An image taken at a distance · the lesion involves the head or neck, top or side of the foot, back of the hand, arm and leg · the subject is male — 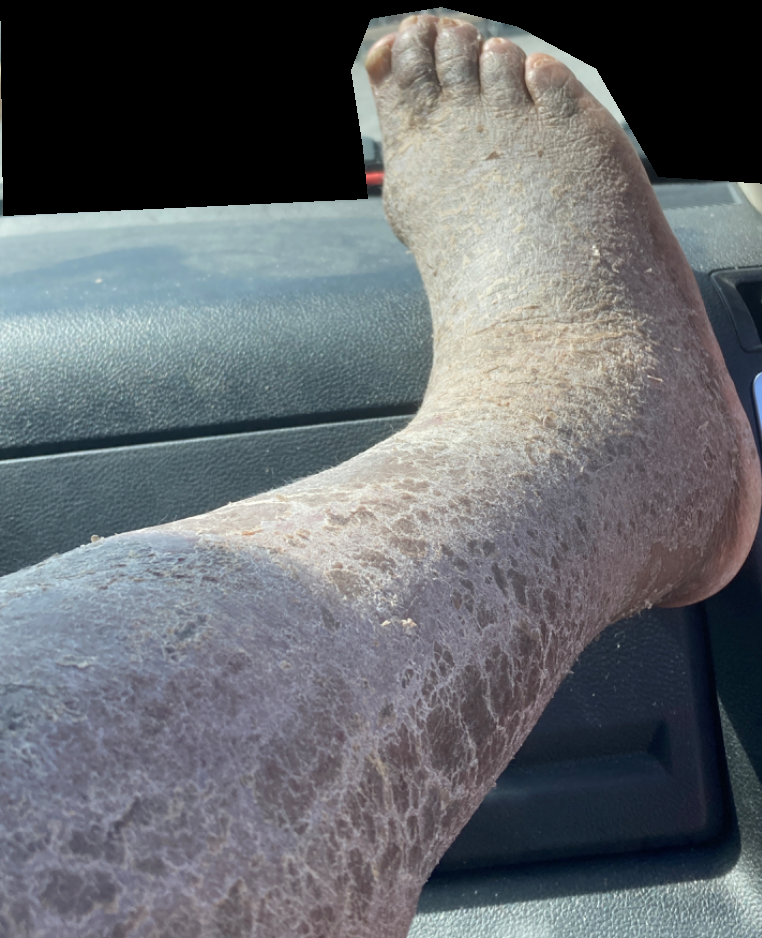| feature | finding |
|---|---|
| systemic symptoms | none reported |
| history | one to three months |
| lesion texture | rough or flaky and fluid-filled |
| skin tone | lay reviewers estimated Monk Skin Tone 1 (US pool) or 2 (India pool) |
| lesion symptoms | bleeding, burning, pain, bothersome appearance, enlargement and itching |
| diagnostic considerations | consistent with Ichthyosis |